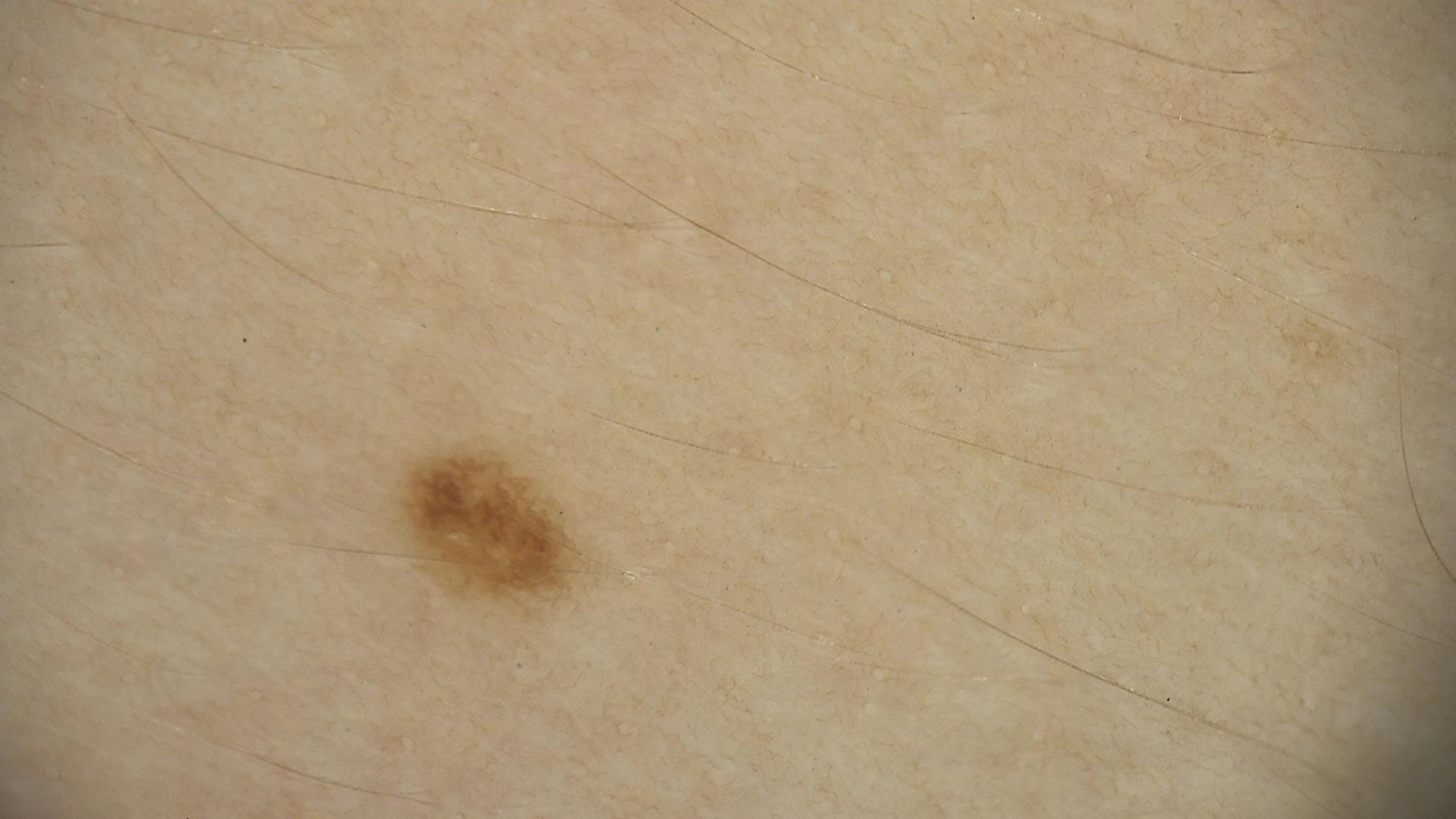imaging: dermoscopy; subtype: banal; diagnosis: junctional nevus (expert consensus).